Reported duration is about one day · skin tone: FST IV · located on the leg · the patient indicates burning and itching · a close-up photograph · no relevant systemic symptoms · texture is reported as raised or bumpy:
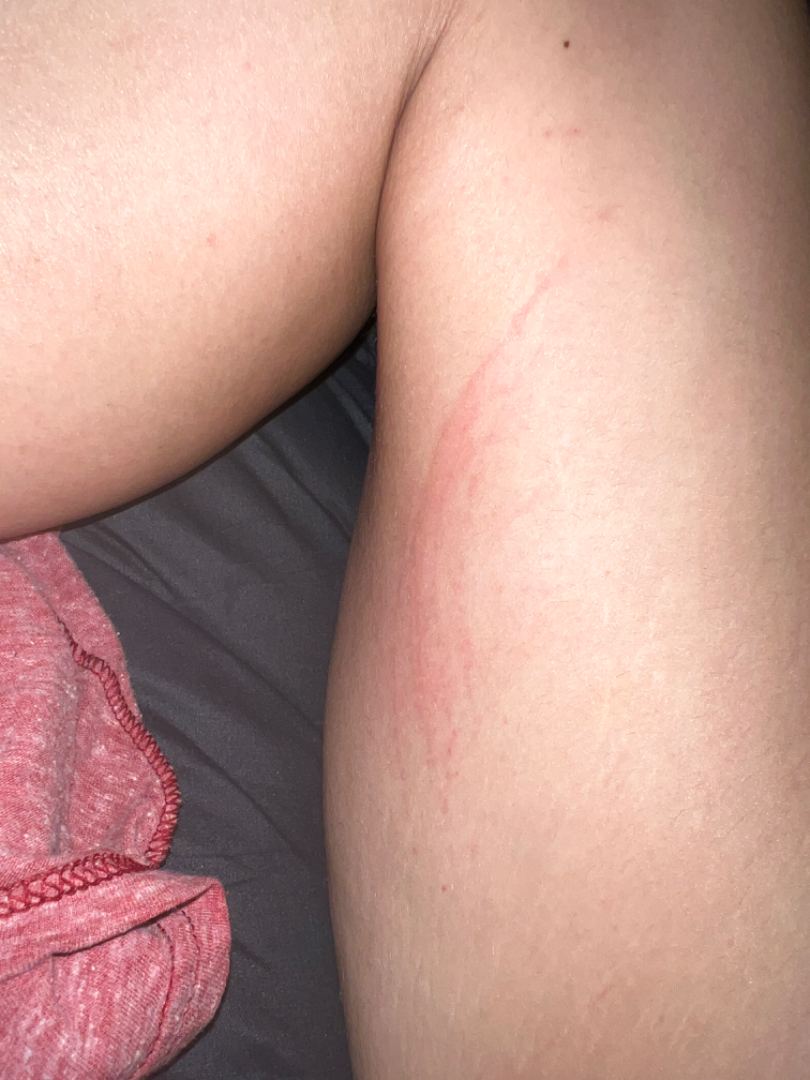assessment: indeterminate.